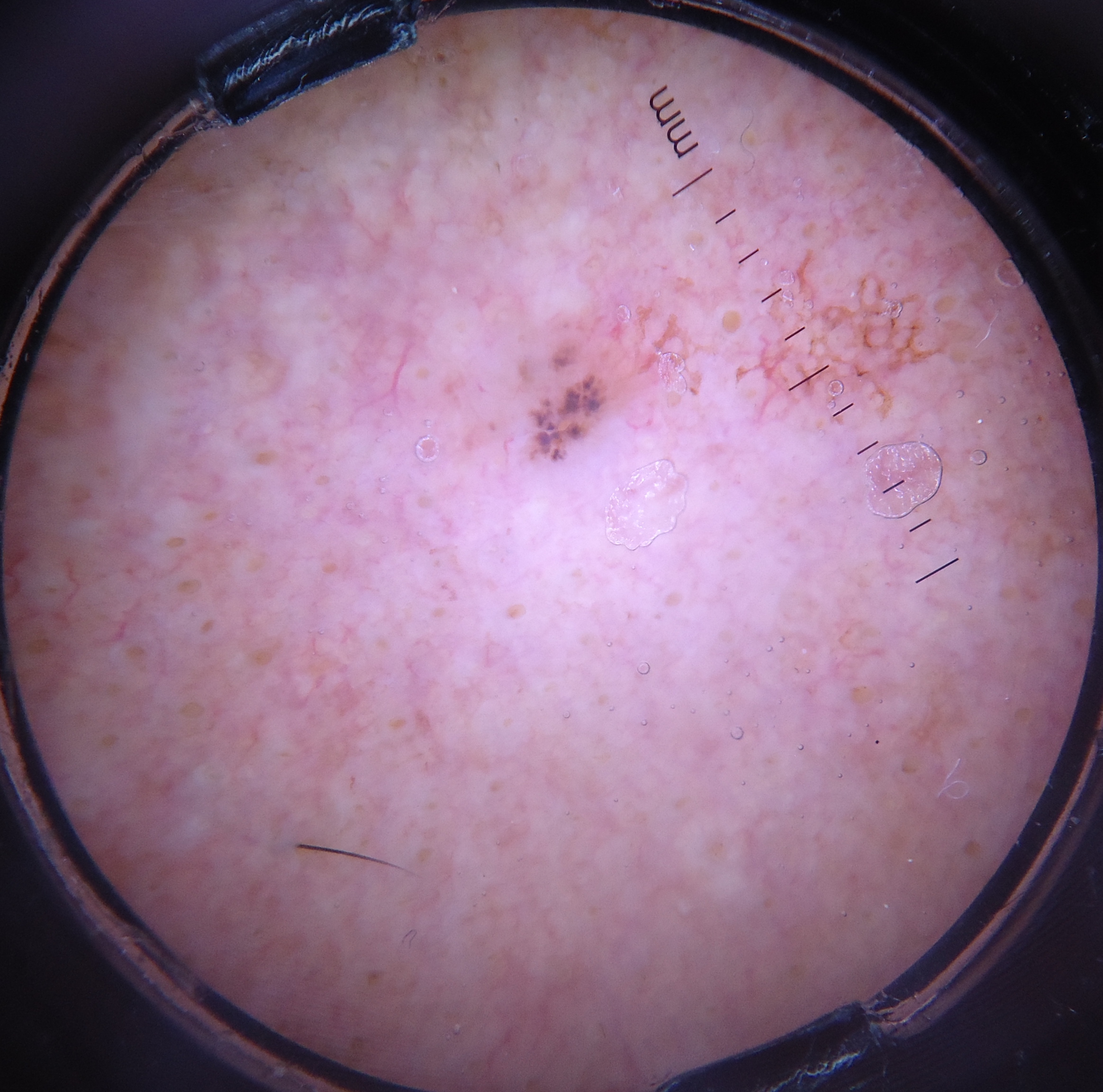<lesion>
<image>dermoscopy</image>
<lesion_type>
<main_class>keratinocytic</main_class>
</lesion_type>
<diagnosis>
<name>basal cell carcinoma</name>
<code>bcc</code>
<malignancy>malignant</malignancy>
<super_class>non-melanocytic</super_class>
<confirmation>histopathology</confirmation>
</diagnosis>
</lesion>